This is a close-up image — 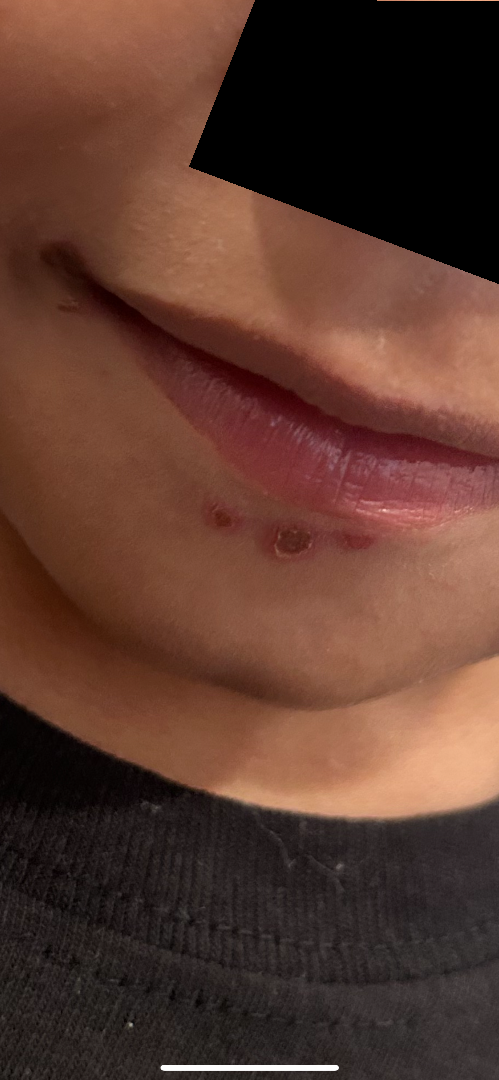On photographic review by a dermatologist: most likely Impetigo.